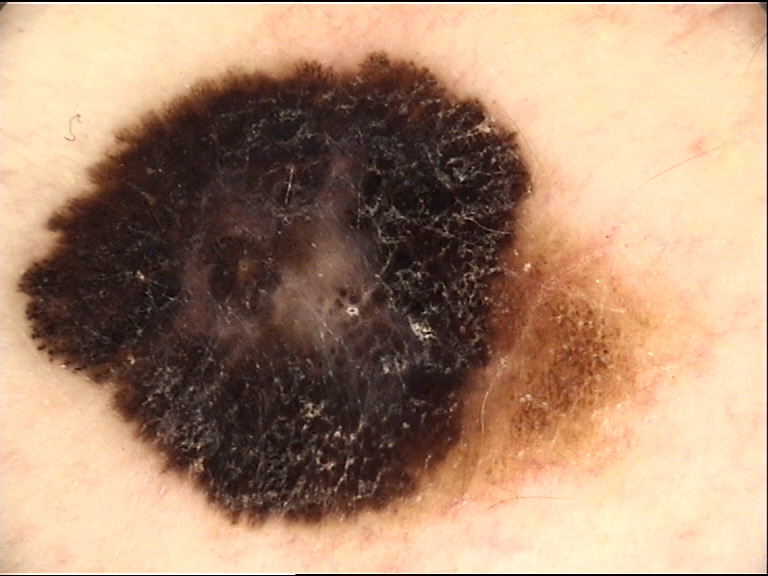Q: What did the workup show?
A: melanoma (biopsy-proven)